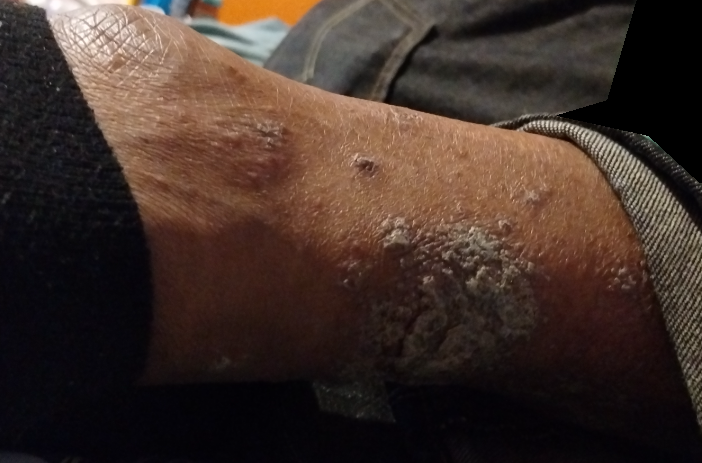The patient reported no systemic symptoms. This image was taken at a distance. The patient considered this a rash. The affected area is the arm, leg, back of the hand and top or side of the foot. The lesion is associated with bleeding, bothersome appearance, itching, enlargement and darkening. The contributor reports the lesion is rough or flaky and raised or bumpy. The subject is 40–49, male. Psoriasis (primary); Lichen planus/lichenoid eruption (possible); Scabies (lower probability).